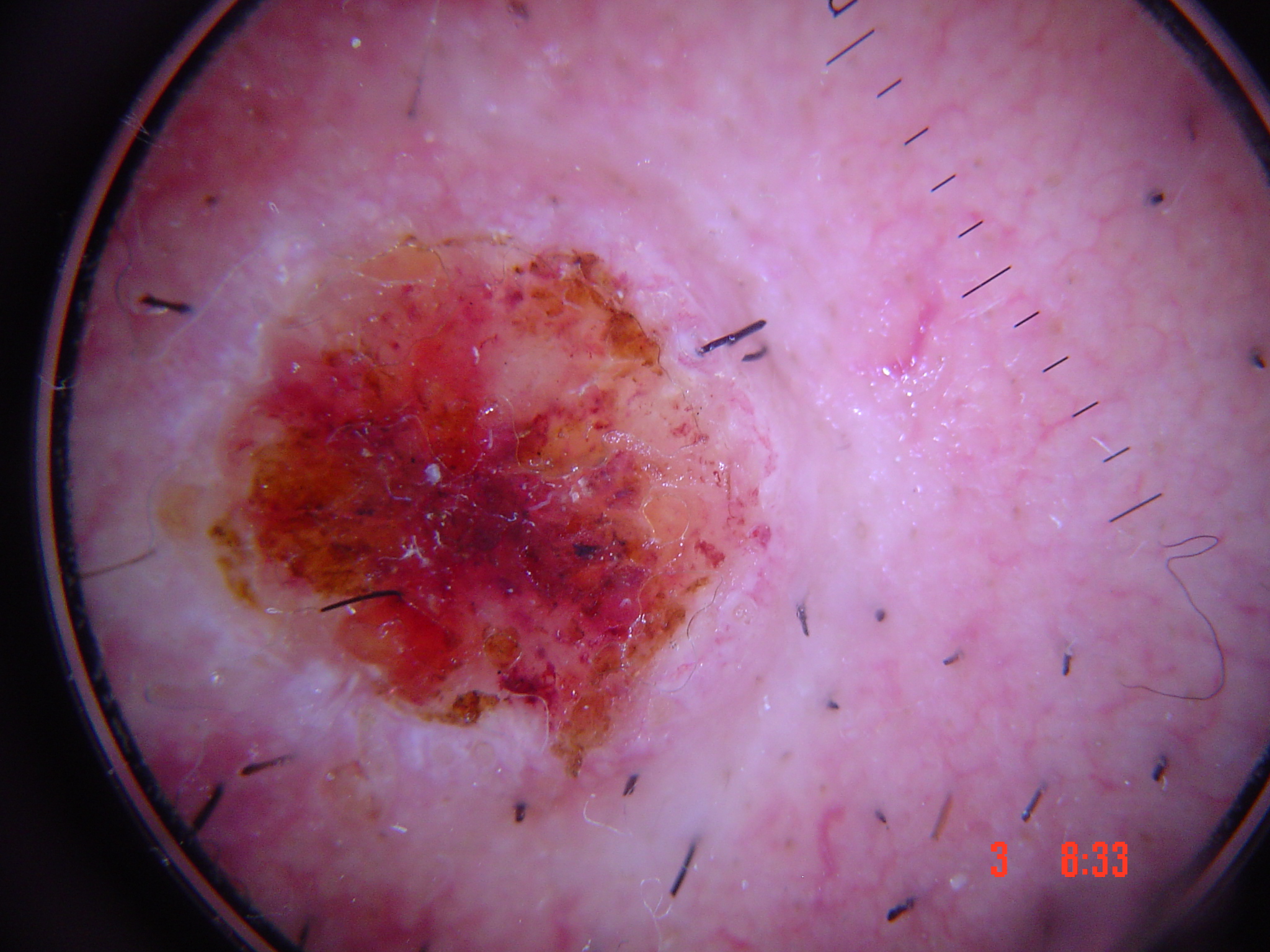Findings: A dermatoscopic image of a skin lesion. This is a keratinocytic lesion. Diagnosis: Confirmed on histopathology as a squamous cell carcinoma.